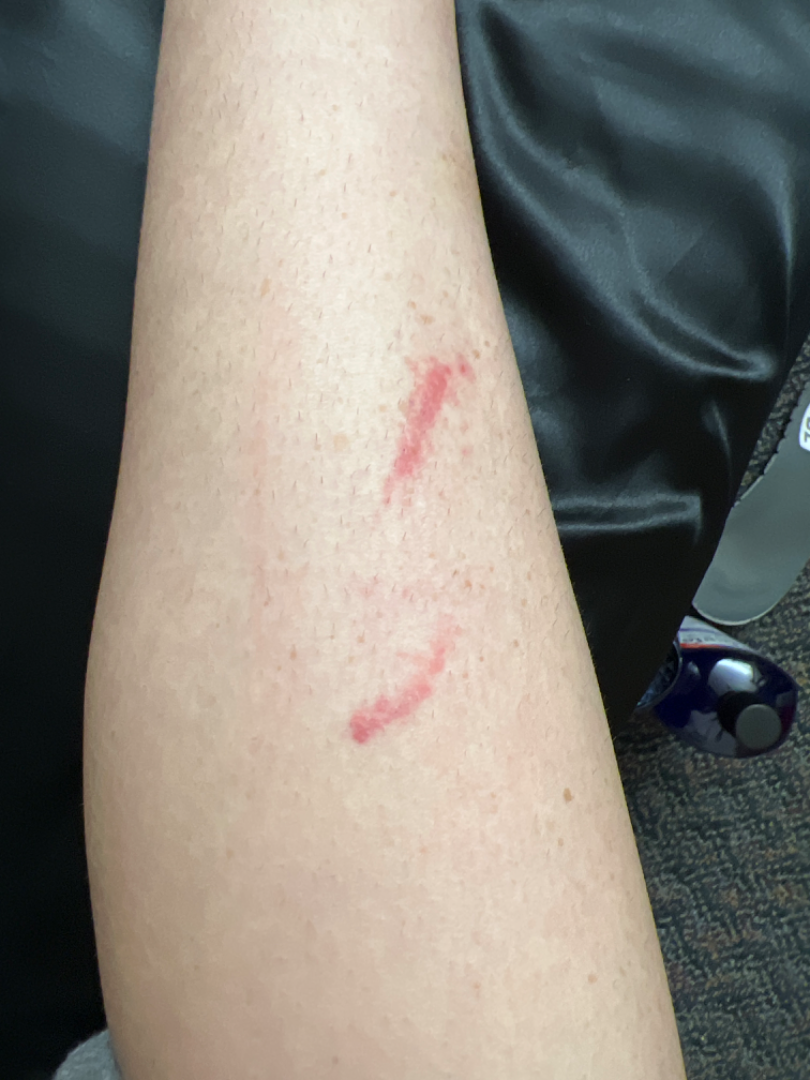Female contributor, age 18–29. The affected area is the leg. Close-up view. The patient reported no systemic symptoms. On photographic review, most likely Allergic Contact Dermatitis; an alternative is Eczema.